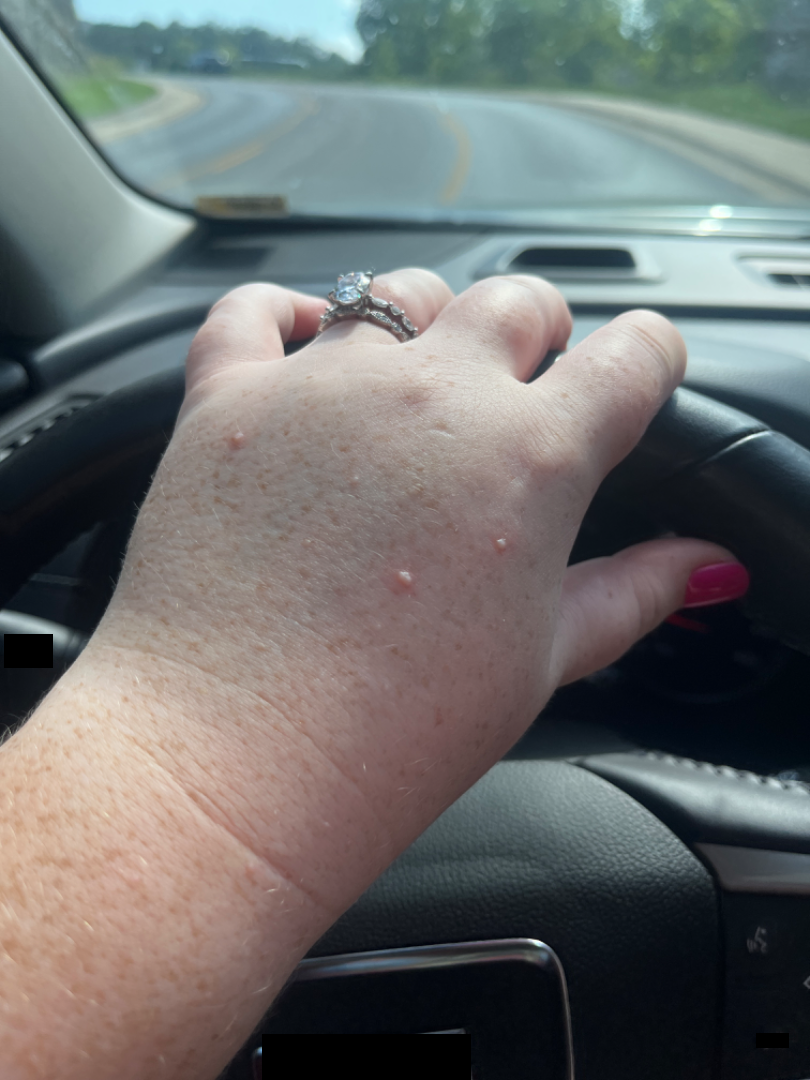<dermatology_case>
<assessment>ungradable on photographic review</assessment>
</dermatology_case>